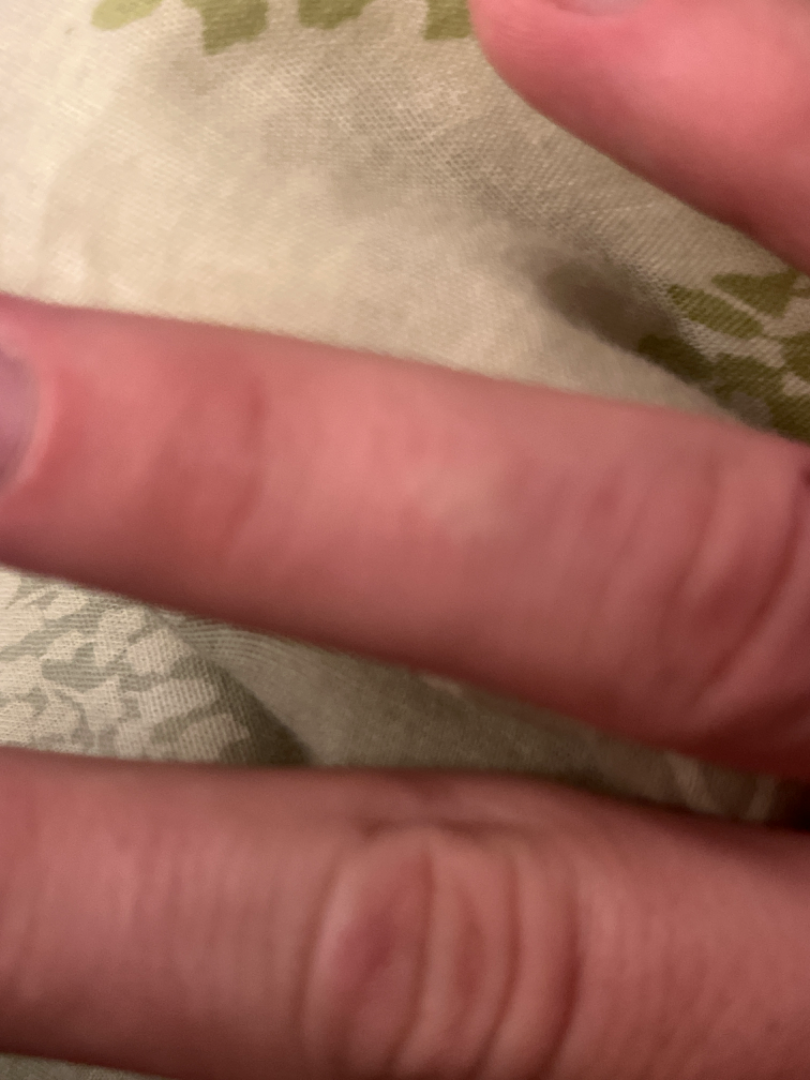assessment — unable to determine.